A skin lesion imaged with a dermatoscope.
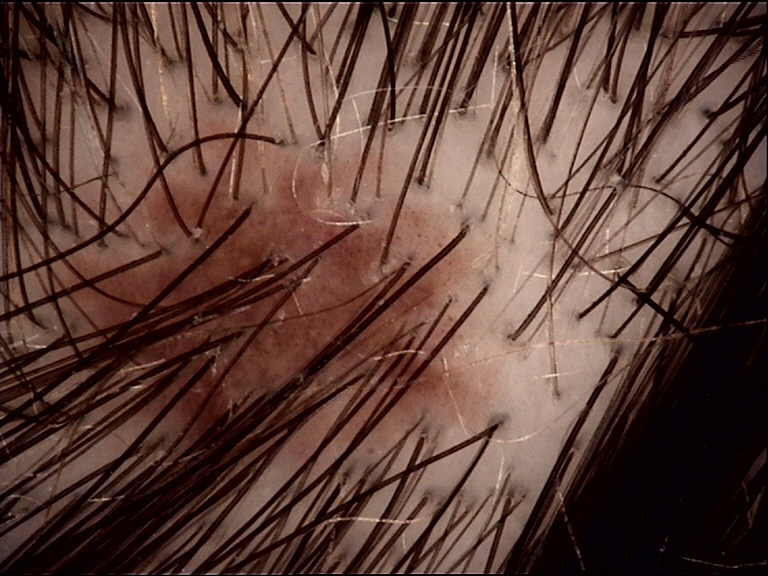Q: What is this lesion?
A: dysplastic junctional nevus (expert consensus)